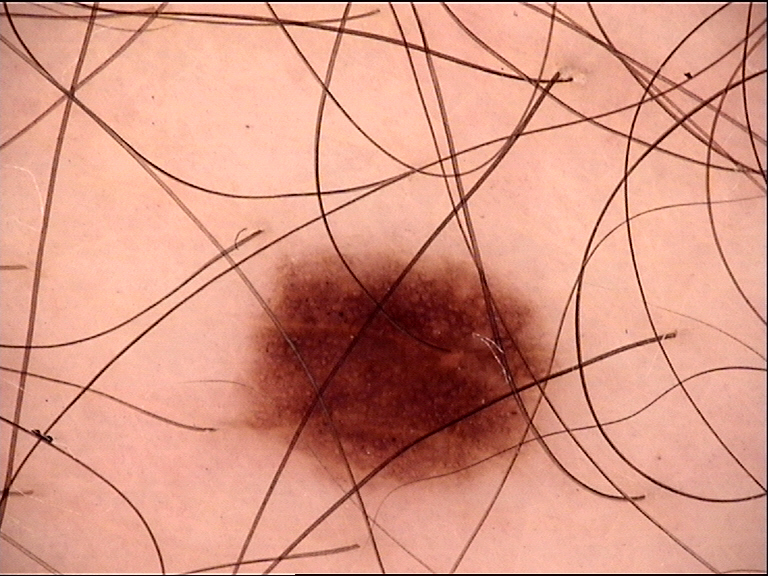{"diagnosis": {"name": "dysplastic junctional nevus", "code": "jd", "malignancy": "benign", "super_class": "melanocytic", "confirmation": "expert consensus"}}